An image taken at an angle; the contributor is 50–59, female; the lesion involves the front of the torso and back of the torso.
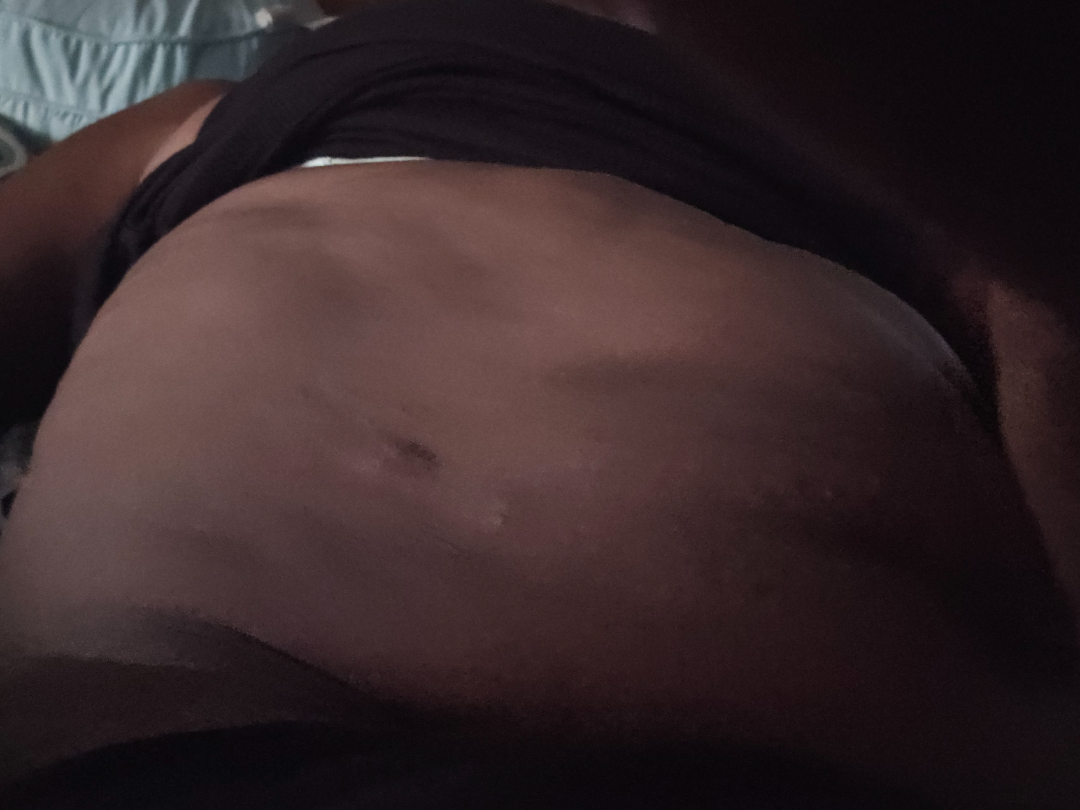The skin findings could not be characterized from the image. The patient notes the lesion is raised or bumpy. The patient notes the condition has been present for one to four weeks. The lesion is associated with itching. The patient described the issue as a rash. The patient notes associated joint pain and fatigue.